The condition has been present for about one day · the photograph is a close-up of the affected area · the affected area is the leg · Fitzpatrick IV:
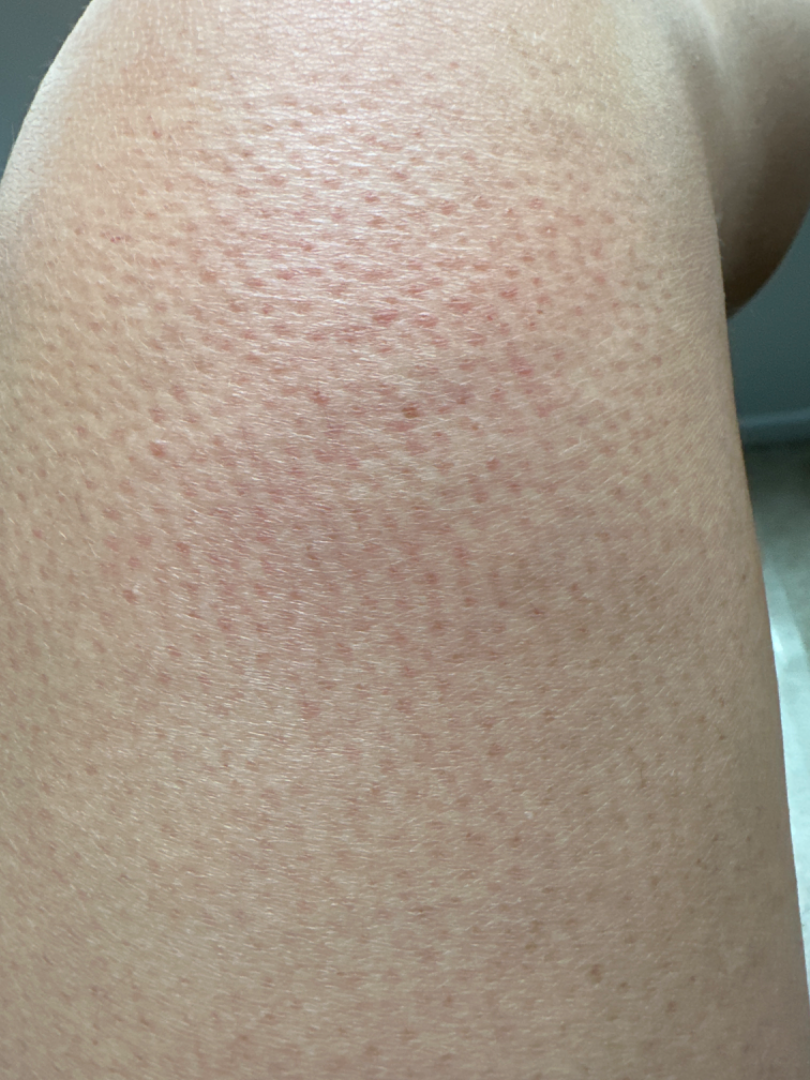Findings:
* clinical impression · Irritant Contact Dermatitis (leading)